A dermoscopic image of a skin lesion.
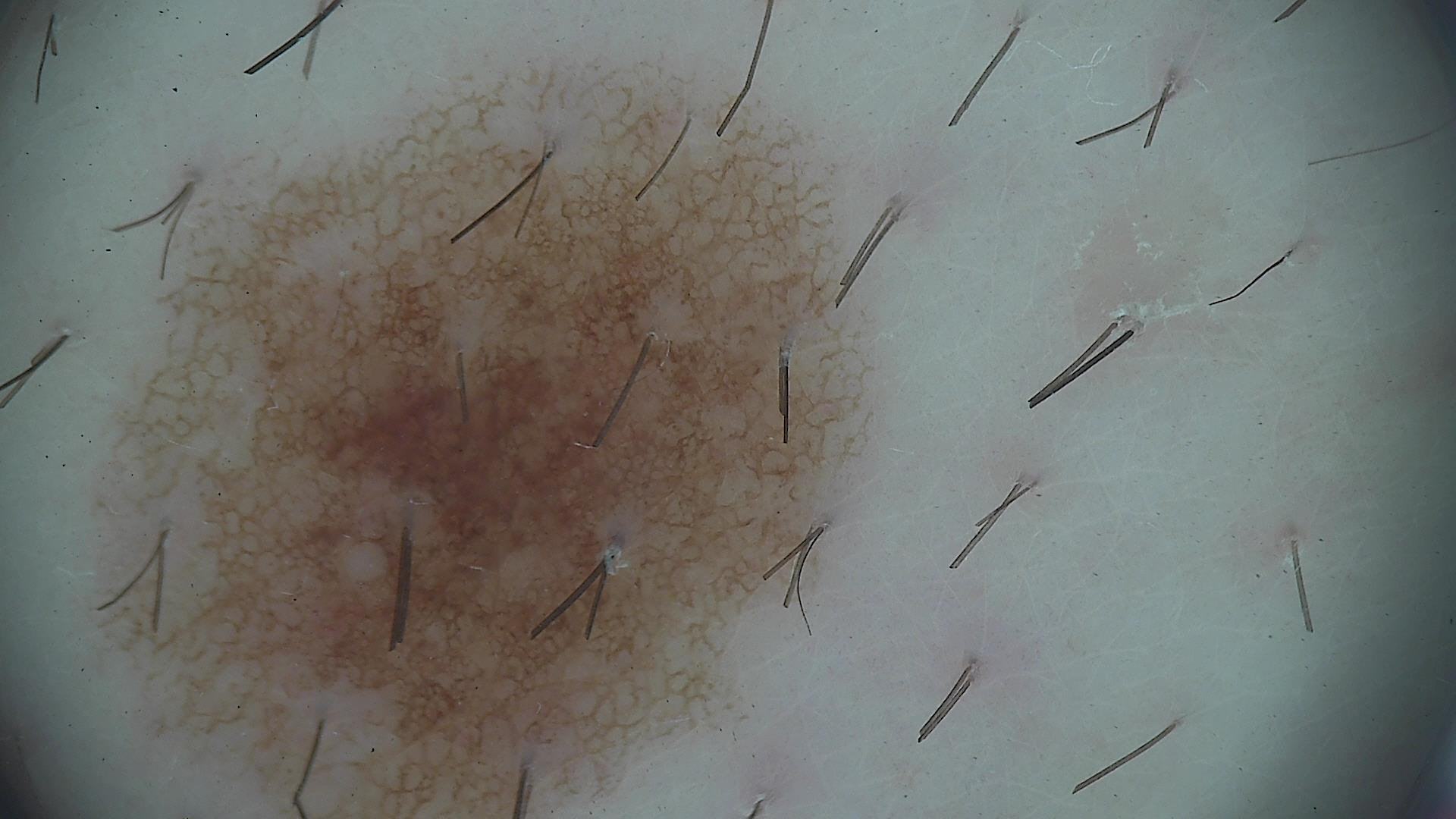label = dysplastic junctional nevus (expert consensus).